A dermoscopic close-up of a skin lesion.
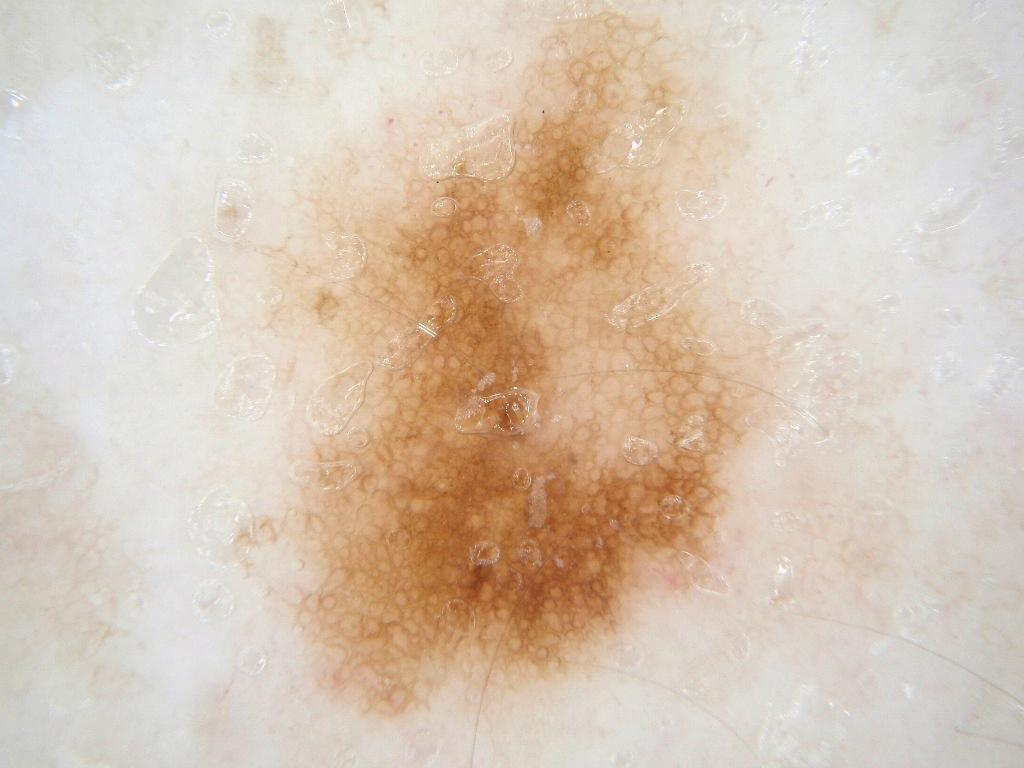The lesion is bounded by x1=214, y1=6, x2=826, y2=742. Expert review diagnosed this as a benign skin lesion.